Acquired for a research image collection, with no referral diagnosis; a male subject aged 73; a clinical photograph showing a skin lesion — 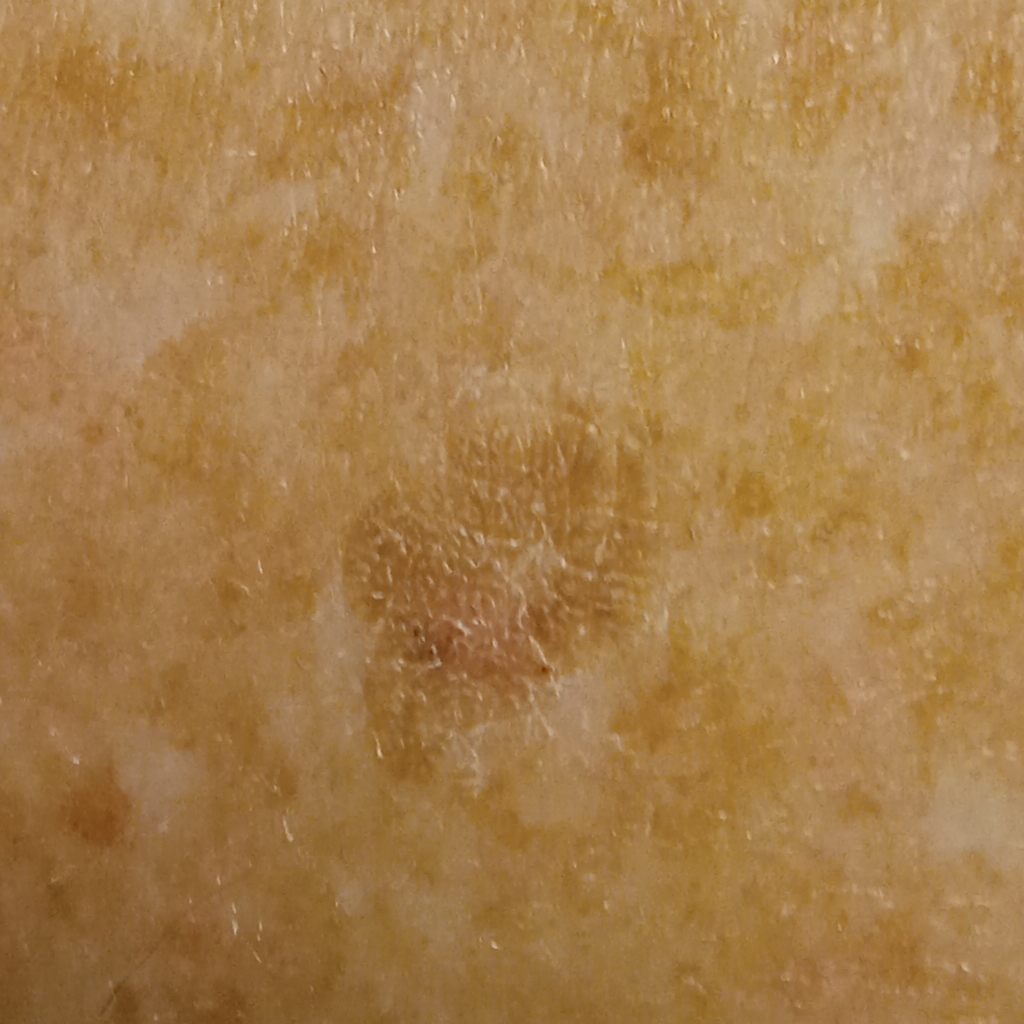The lesion involves the back. The lesion measures approximately 10.7 mm. Dermatologist review favored a seborrheic keratosis.